A dermoscopic photograph of a skin lesion.
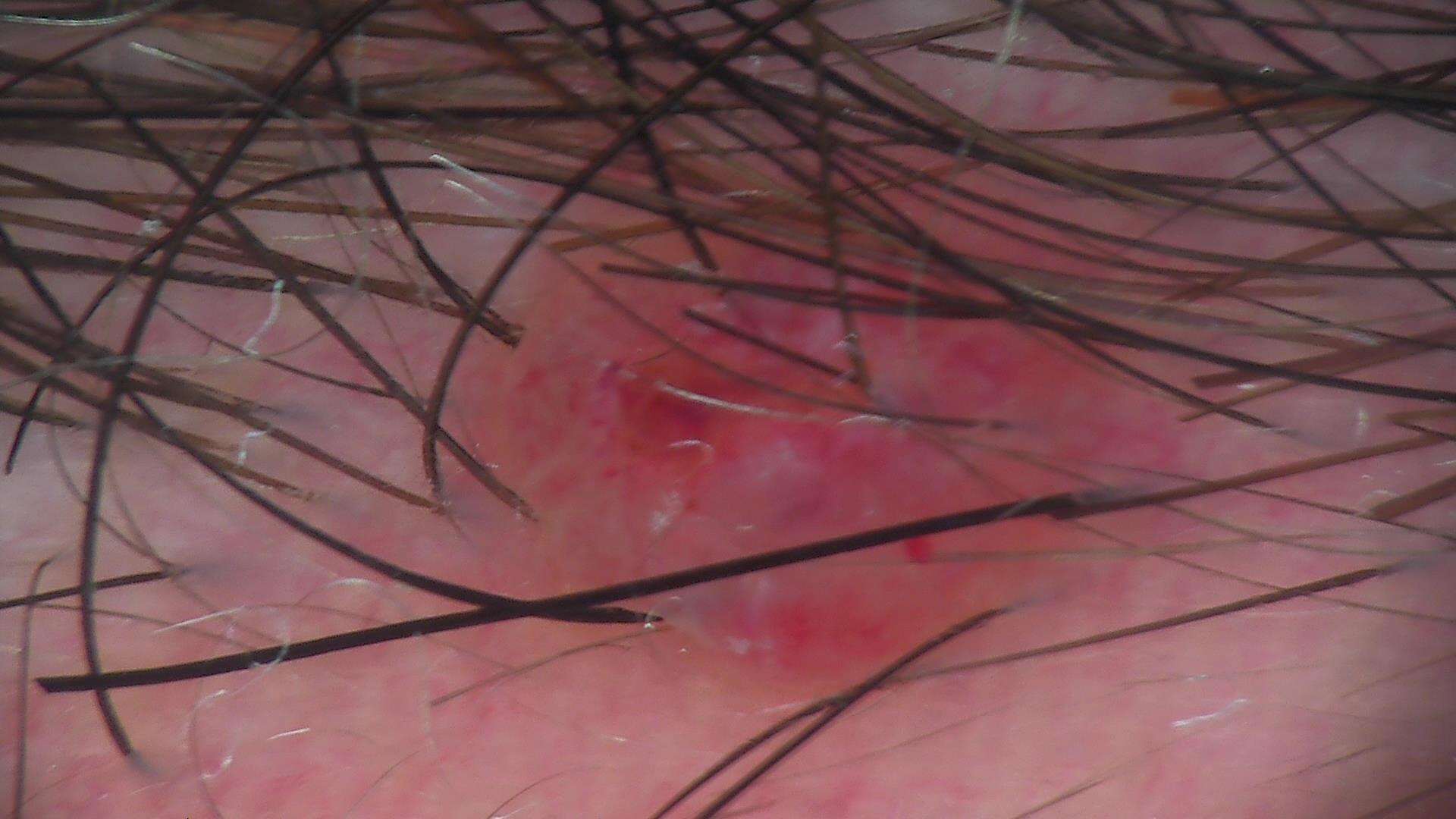Summary:
The architecture is that of a banal lesion.
Conclusion:
The diagnosis was a dermal nevus.